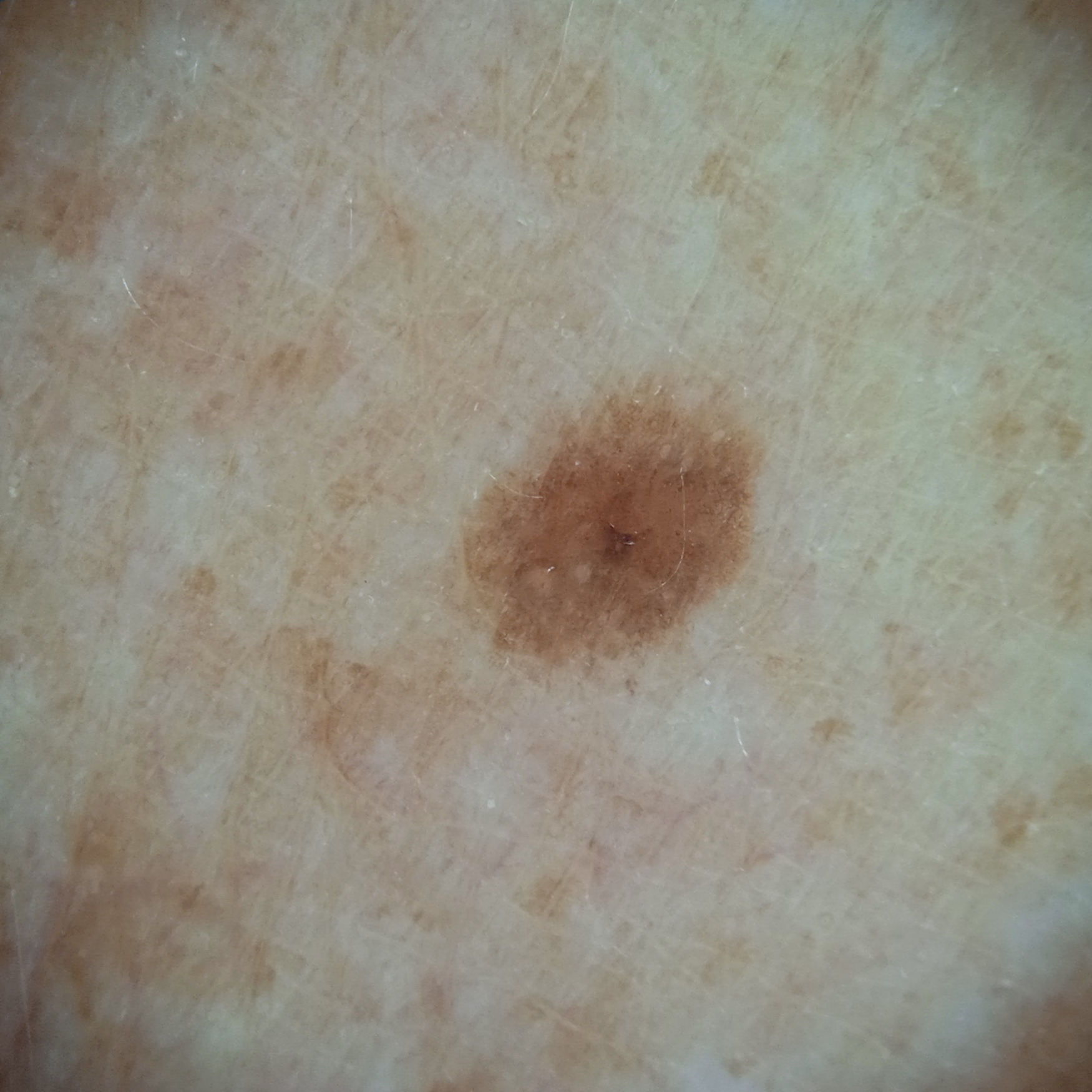By self-report, no personal history of cancer and no sunbed use. A male patient 72 years old. Acquired for a research image collection, with no referral diagnosis. A dermoscopic image of a skin lesion. The patient says their skin tans without first burning. The lesion is on the back. The lesion is about 3.7 mm across. The diagnostic impression was a melanocytic nevus.